A dermoscopic close-up of a skin lesion · the patient is a male aged 63-67.
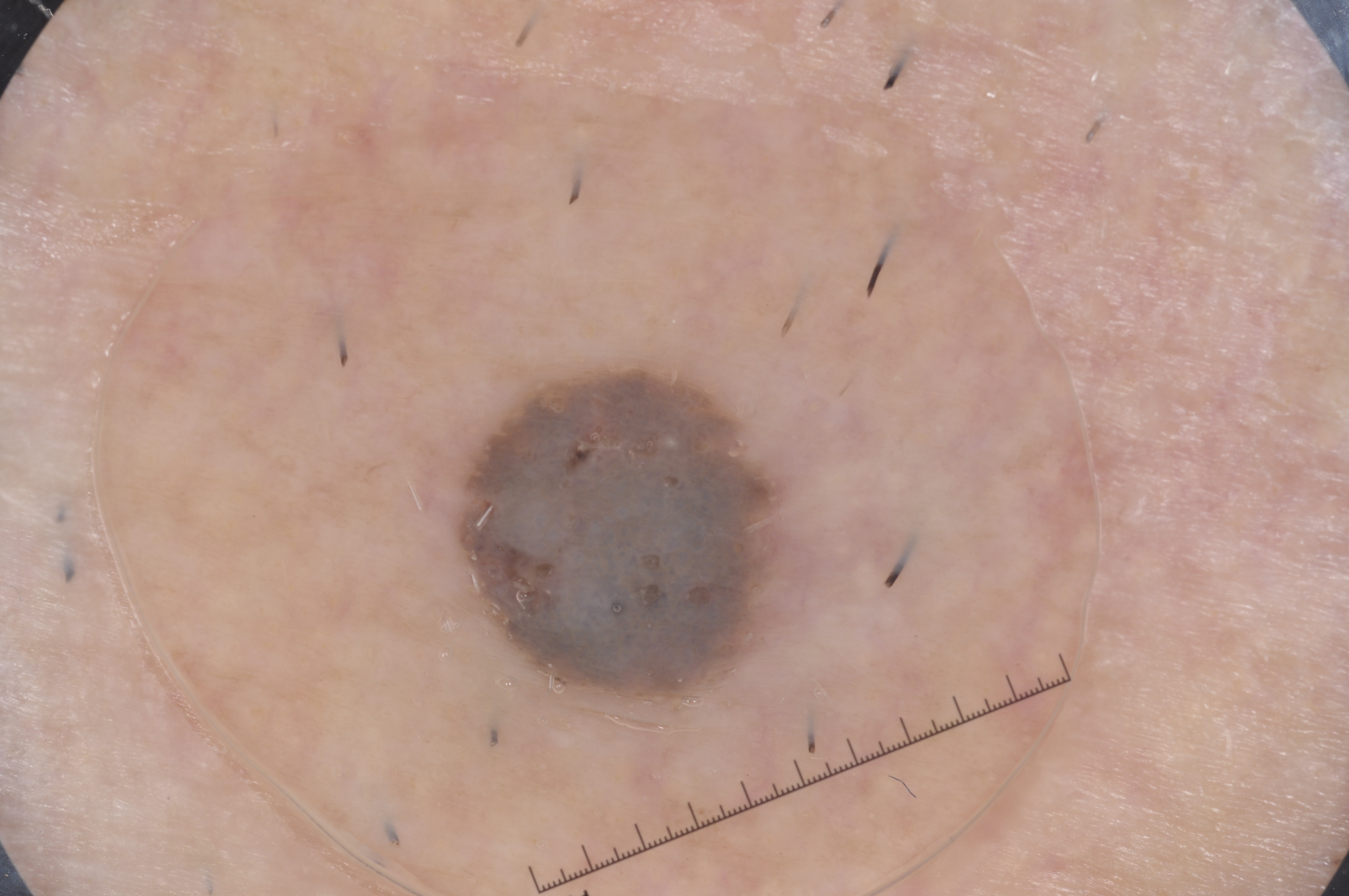{
  "lesion_location": {
    "bbox_xyxy": [
      433,
      350,
      811,
      707
    ]
  },
  "lesion_extent": "moderate",
  "dermoscopic_features": {
    "present": [
      "milia-like cysts"
    ],
    "absent": [
      "streaks",
      "pigment network",
      "negative network"
    ]
  },
  "diagnosis": {
    "name": "seborrheic keratosis",
    "malignancy": "benign",
    "lineage": "keratinocytic",
    "provenance": "clinical"
  }
}